The patient is a male roughly 15 years of age · a dermoscopy image of a single skin lesion:
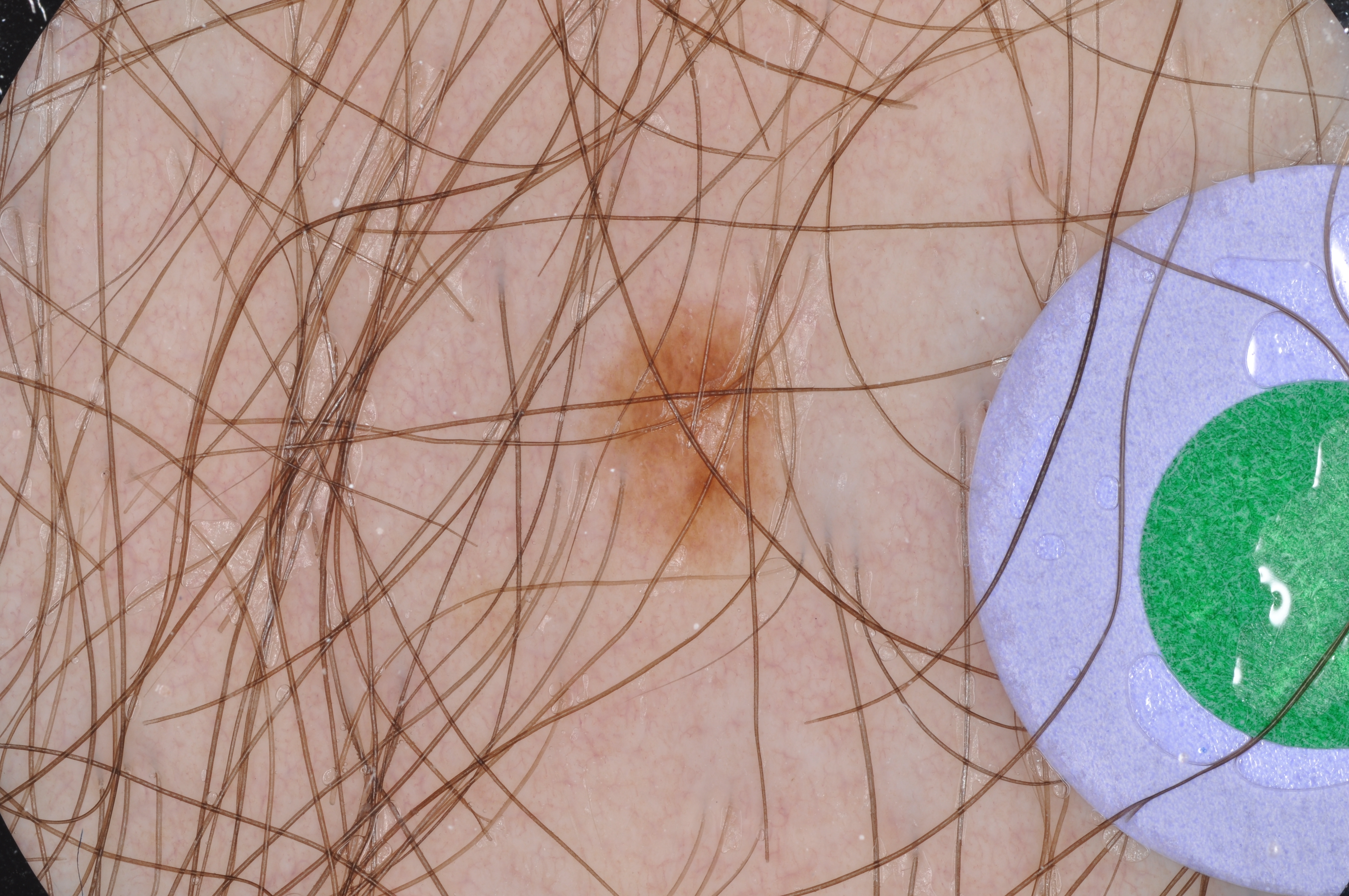In (x1, y1, x2, y2) order, the lesion spans <box>581, 290, 804, 567</box>. Dermoscopically, the lesion shows no negative network, milia-like cysts, streaks, globules, or pigment network. The clinical diagnosis was a melanocytic nevus, a benign skin lesion.